The lesion involves the arm. The photograph is a close-up of the affected area — 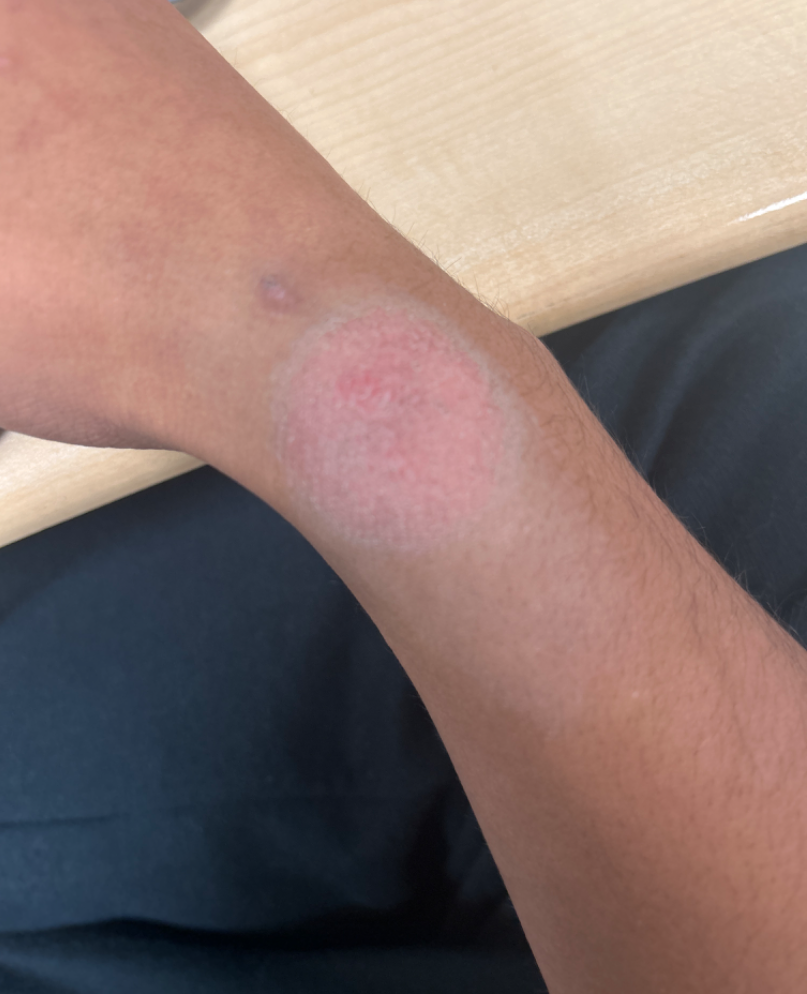differential diagnosis=most likely Allergic Contact Dermatitis; with consideration of Irritant Contact Dermatitis.